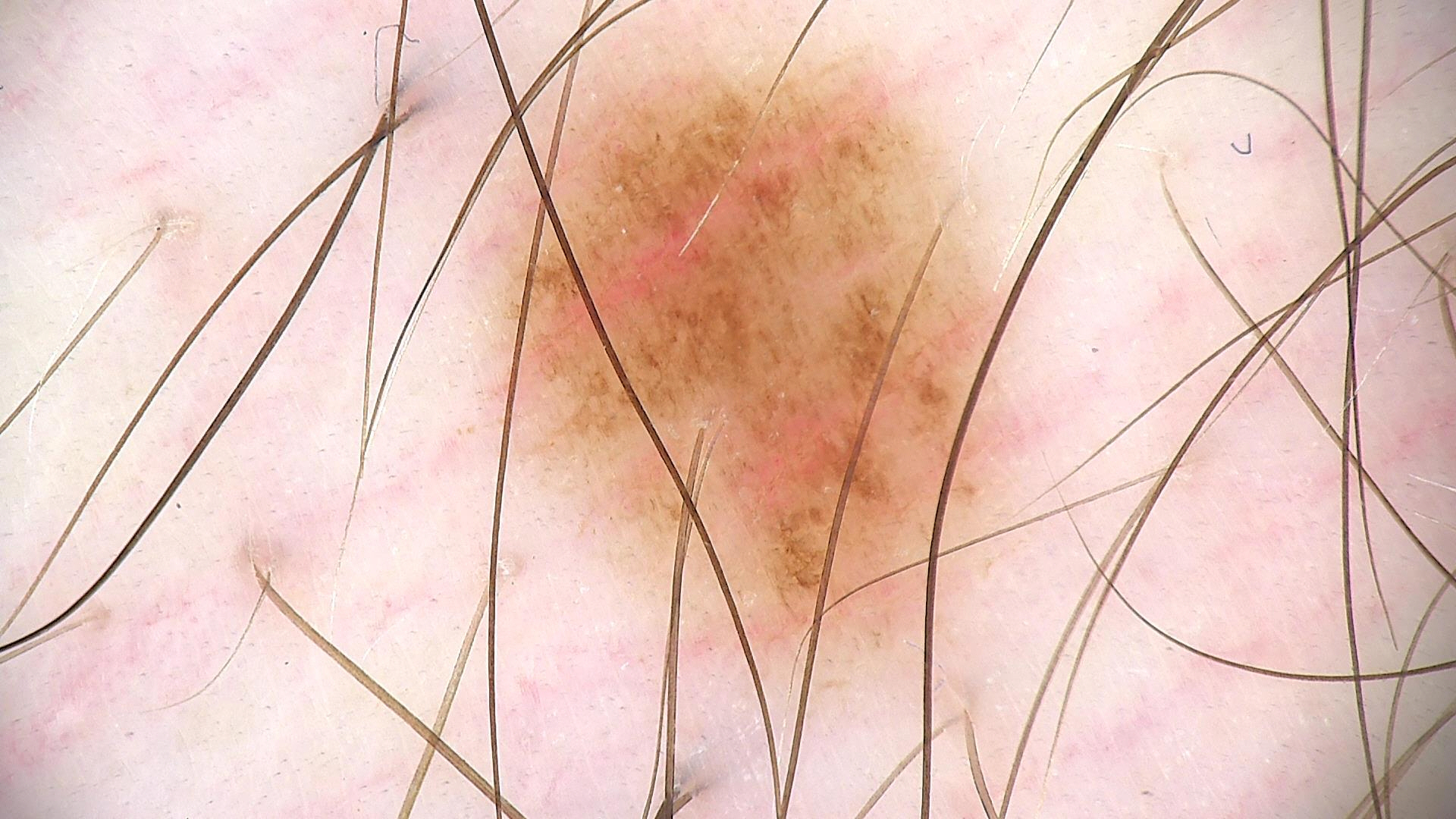Consistent with a dysplastic junctional nevus.